A male subject in their mid-60s · recorded as FST II · by history, prior skin cancer (patient or family) and prior malignancy (patient or family) · a clinical photo of a skin lesion taken with a smartphone.
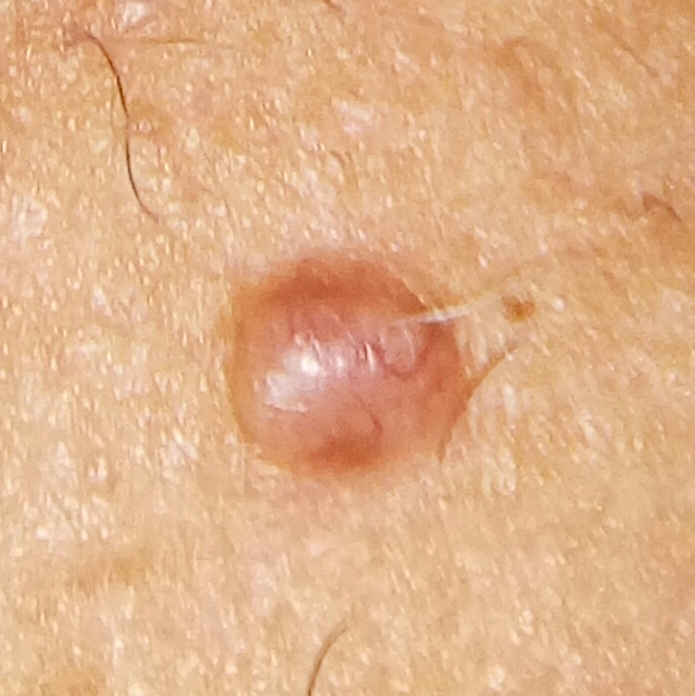body site: the neck; size: 6x4 mm; reported symptoms: elevation, growth / no bleeding; pathology: basal cell carcinoma (biopsy-proven).